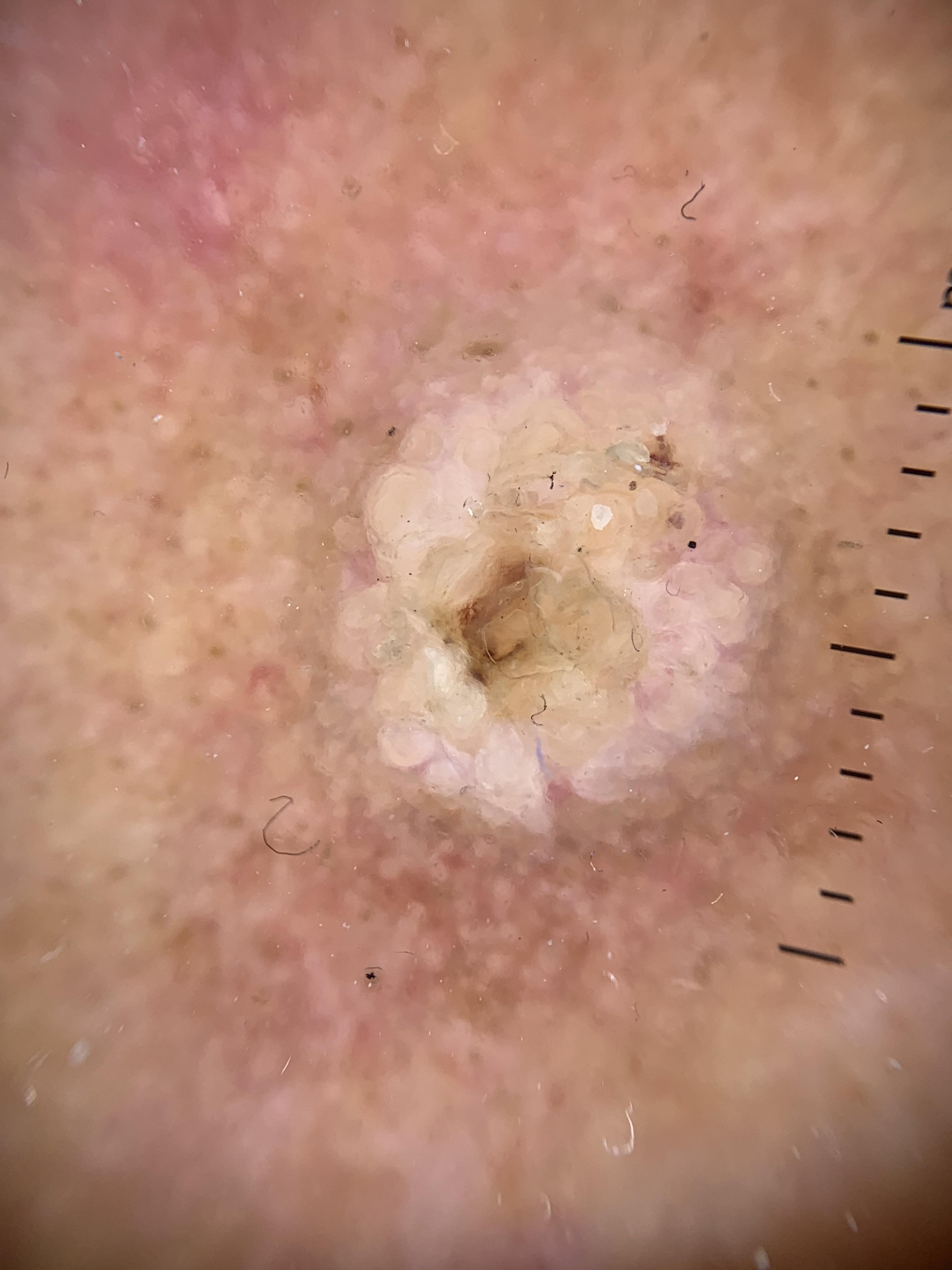A male patient aged approximately 65. A dermoscopy image of a single skin lesion. FST II. The lesion is on the head or neck. Histopathological examination showed a malignant, epidermal lesion — a squamous cell carcinoma.